The photograph was taken at an angle, the subject is a female aged 30–39, the affected area is the back of the hand and arm:
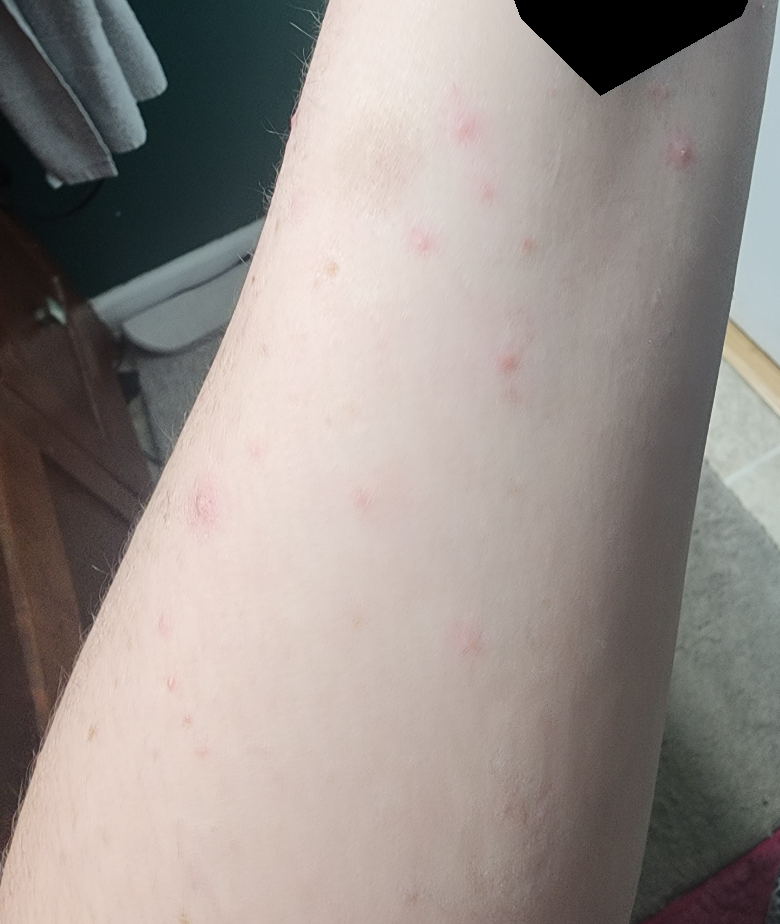Case summary:
* impression: most likely Folliculitis; also consider Insect Bite